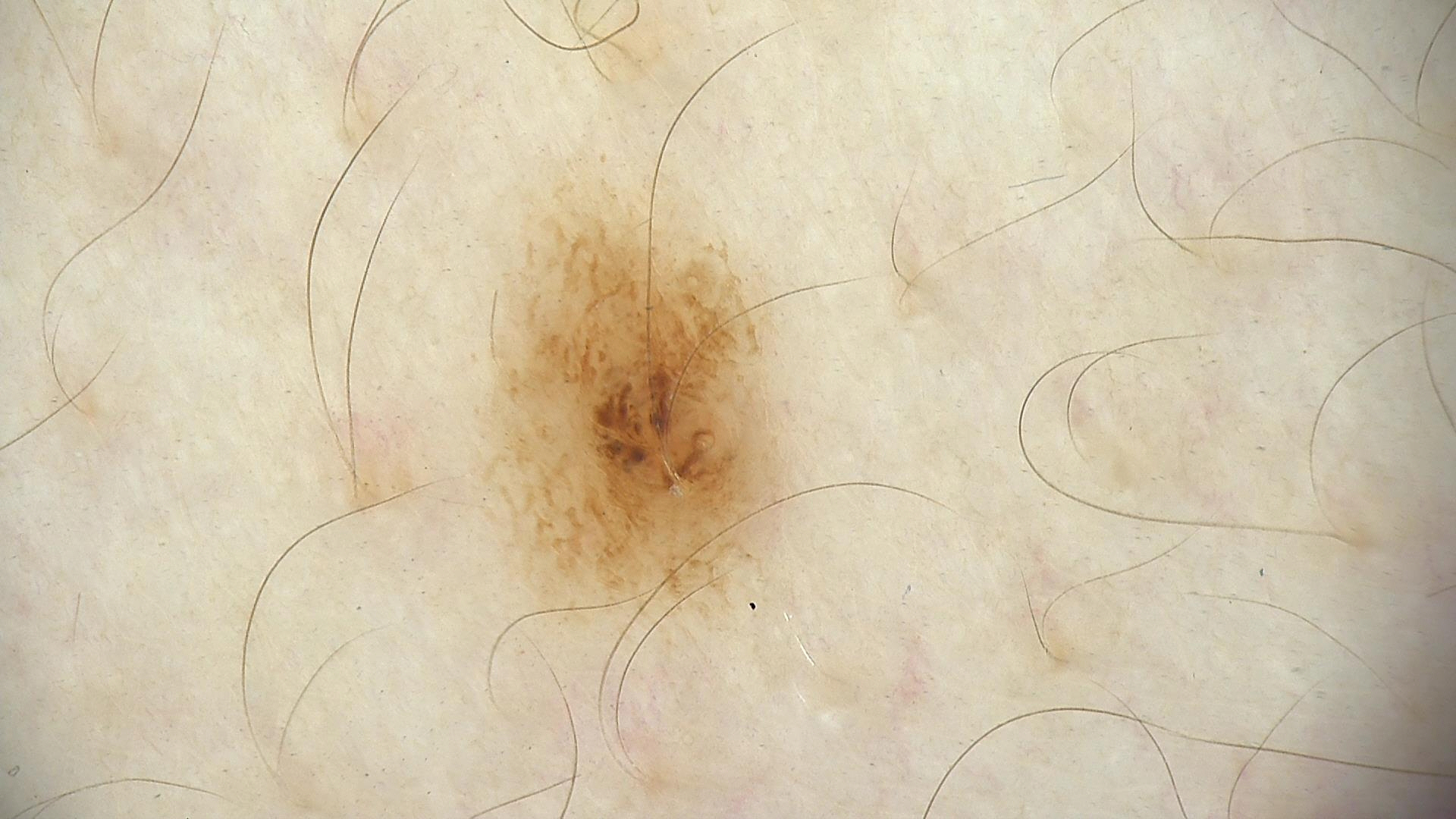| key | value |
|---|---|
| class | dysplastic junctional nevus (expert consensus) |